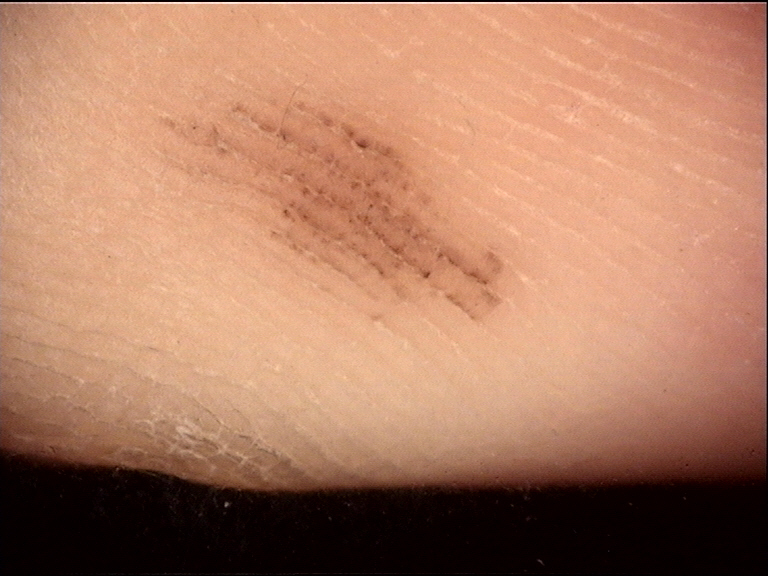– imaging · dermoscopy
– category · banal
– label · acral junctional nevus (expert consensus)